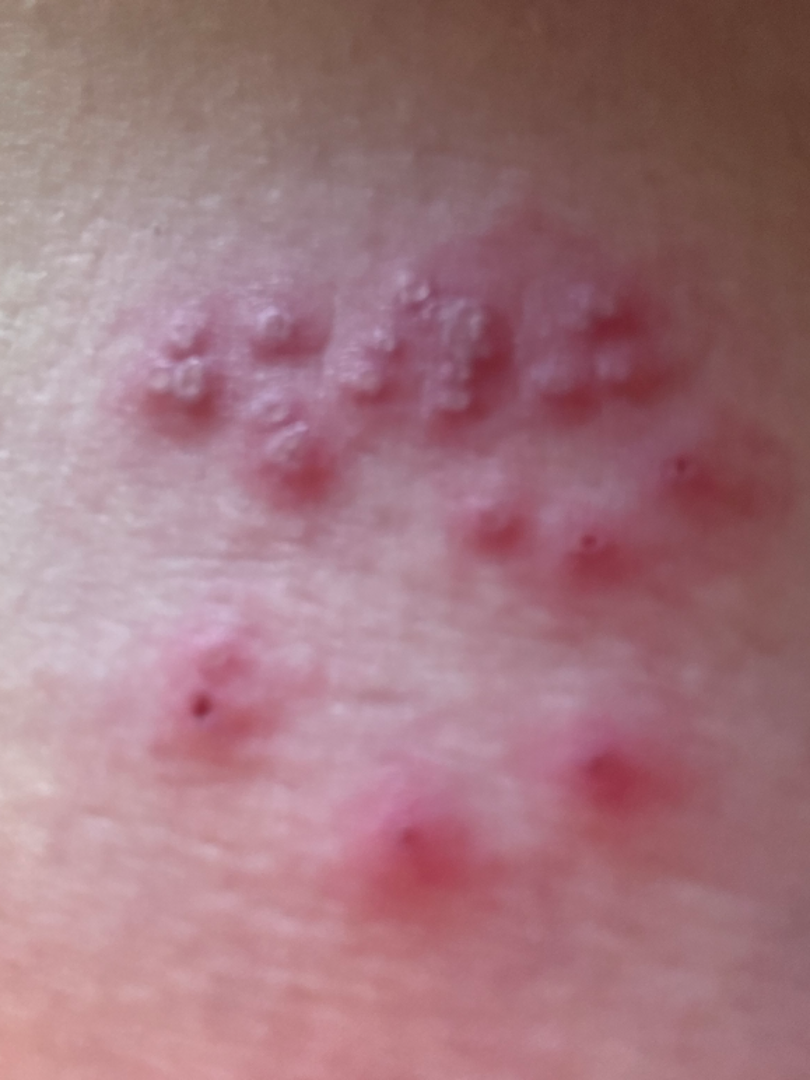Patient information: The patient described the issue as a rash. Present for less than one week. The lesion involves the leg. Female contributor, age 50–59. The lesion is associated with enlargement, pain and burning. A close-up photograph. Review: On photographic review by a dermatologist, Molluscum Contagiosum (favored); Impetigo (considered); Herpes Simplex (considered).